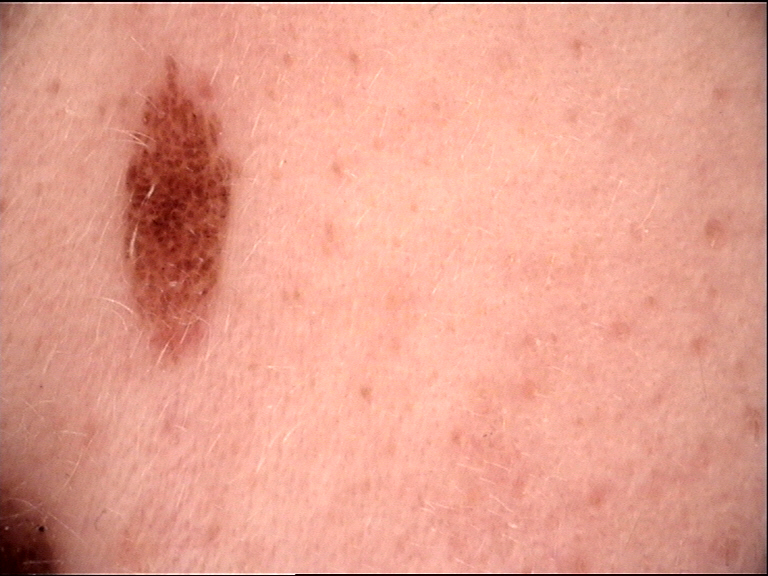Findings:
A dermoscopy image of a single skin lesion.
Impression:
The diagnosis was a banal lesion — a compound nevus.